A skin lesion imaged with a dermatoscope.
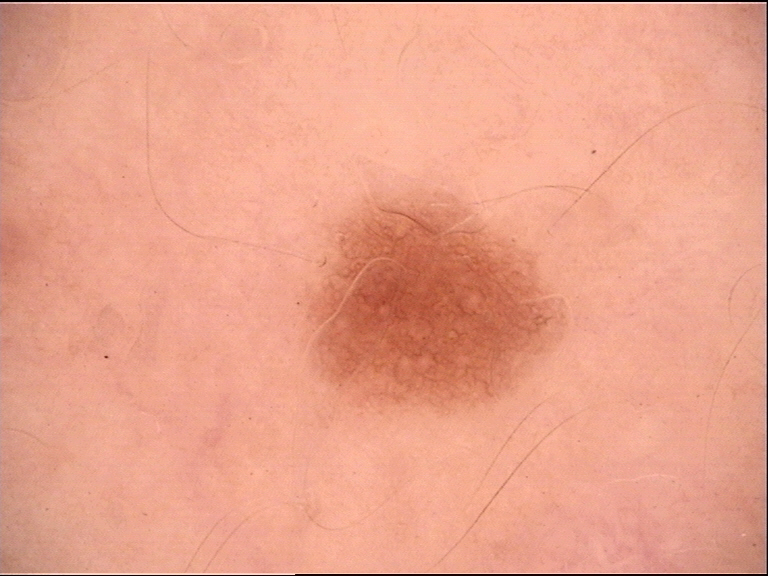{
  "diagnosis": {
    "name": "dysplastic junctional nevus",
    "code": "jd",
    "malignancy": "benign",
    "super_class": "melanocytic",
    "confirmation": "expert consensus"
  }
}